A skin lesion imaged with a dermatoscope. Acquired for a research image collection, with no referral diagnosis. The patient says their skin reddens with sun exposure:
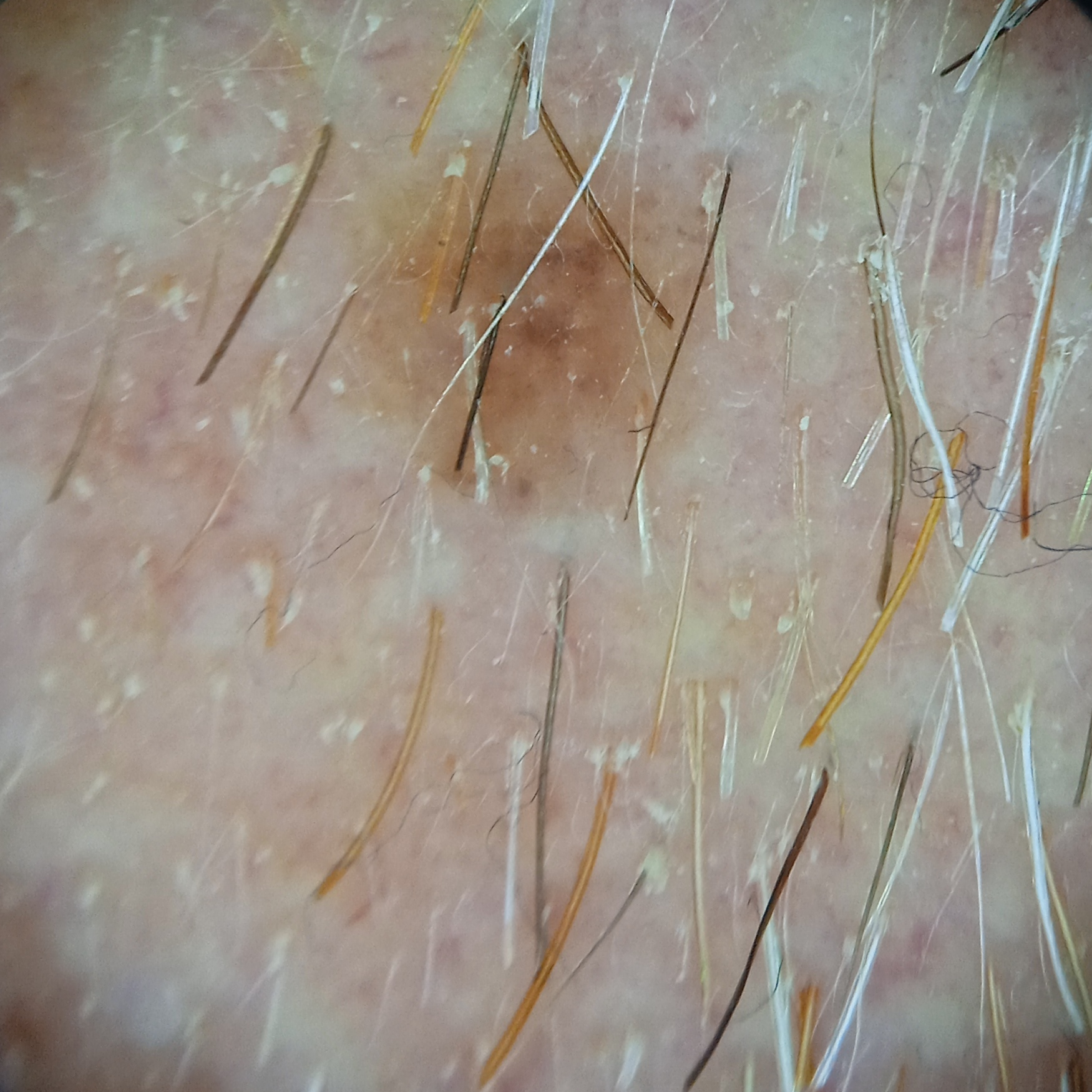Q: What was the diagnosis?
A: melanocytic nevus (dermatologist consensus)